Female subject, age 18–29 · located on the top or side of the foot · this image was taken at a distance · the lesion is described as raised or bumpy · the patient described the issue as skin that appeared healthy to them — 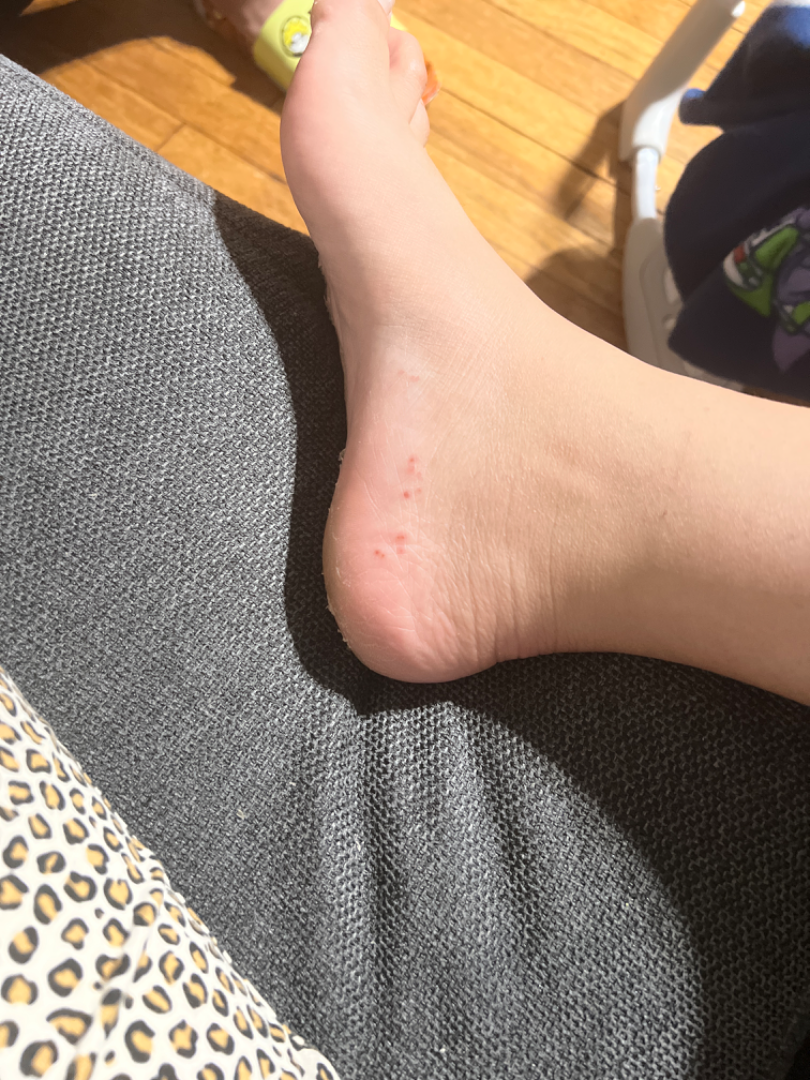Q: What conditions are considered?
A: Tinea (favored); Eczema (possible)